A male subject 73 years of age. A macroscopic clinical photograph of a skin lesion. On a questionnaire the patient reported a personal history of cancer, no immunosuppression, and no prior organ transplant. Numerous moles by the patient's own estimate. Imaged for a research study, with no referral diagnosis recorded. The patient says their skin reddens with sun exposure:
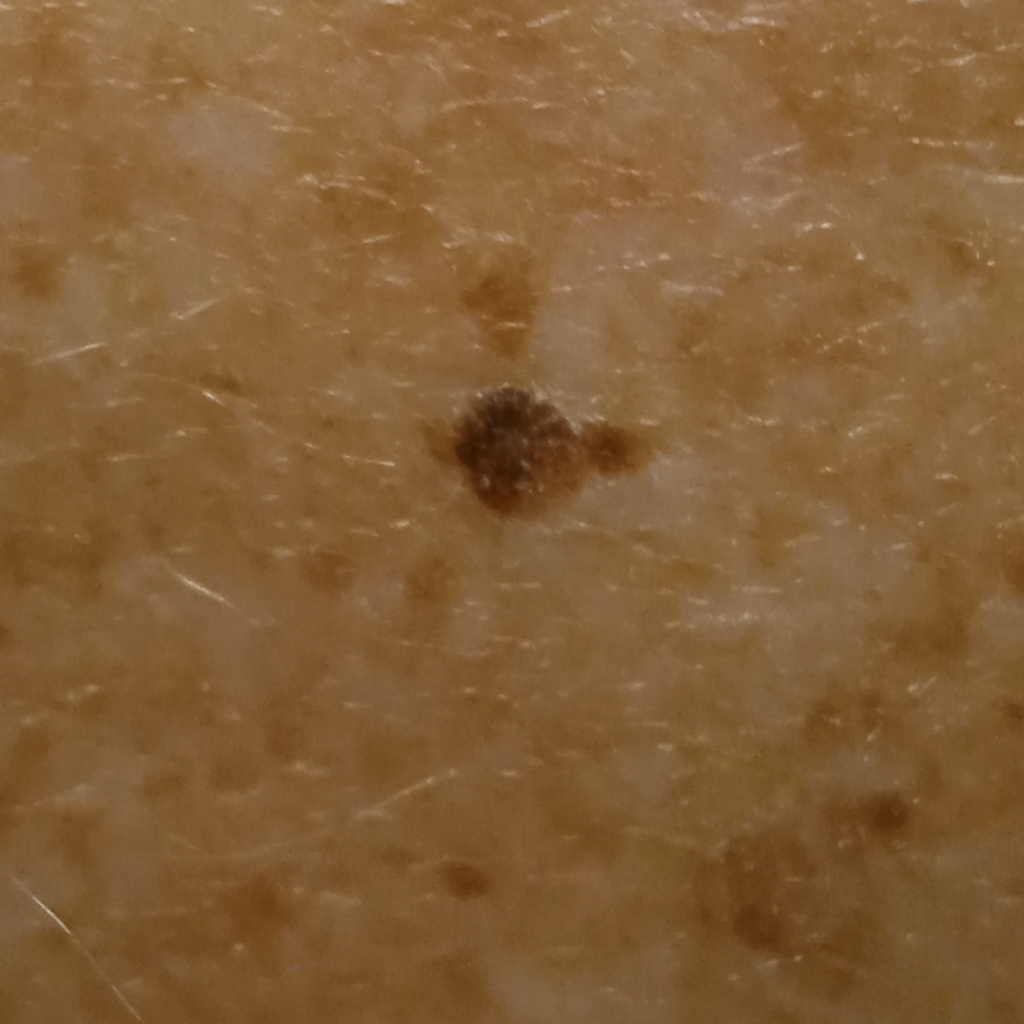{"lesion_location": "the back", "lesion_size": {"diameter_mm": 5.5}, "diagnosis": {"name": "seborrheic keratosis", "malignancy": "benign"}}